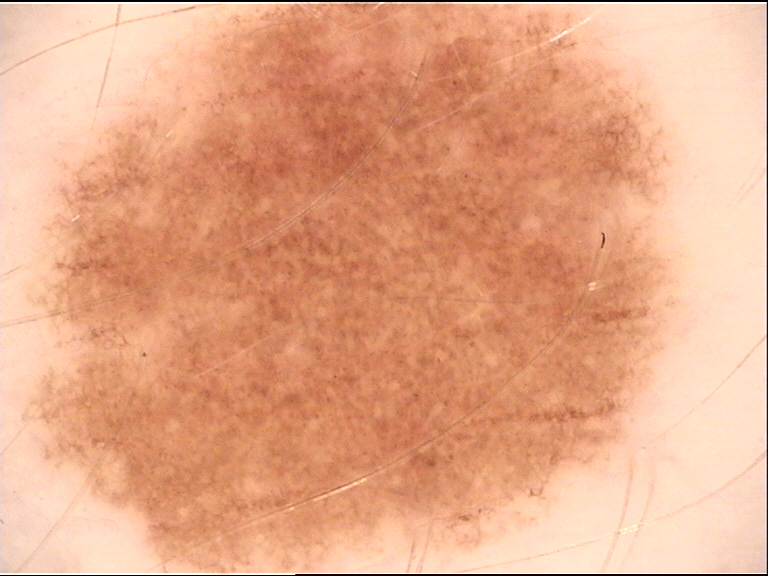Diagnosed as a benign lesion — a dysplastic junctional nevus.